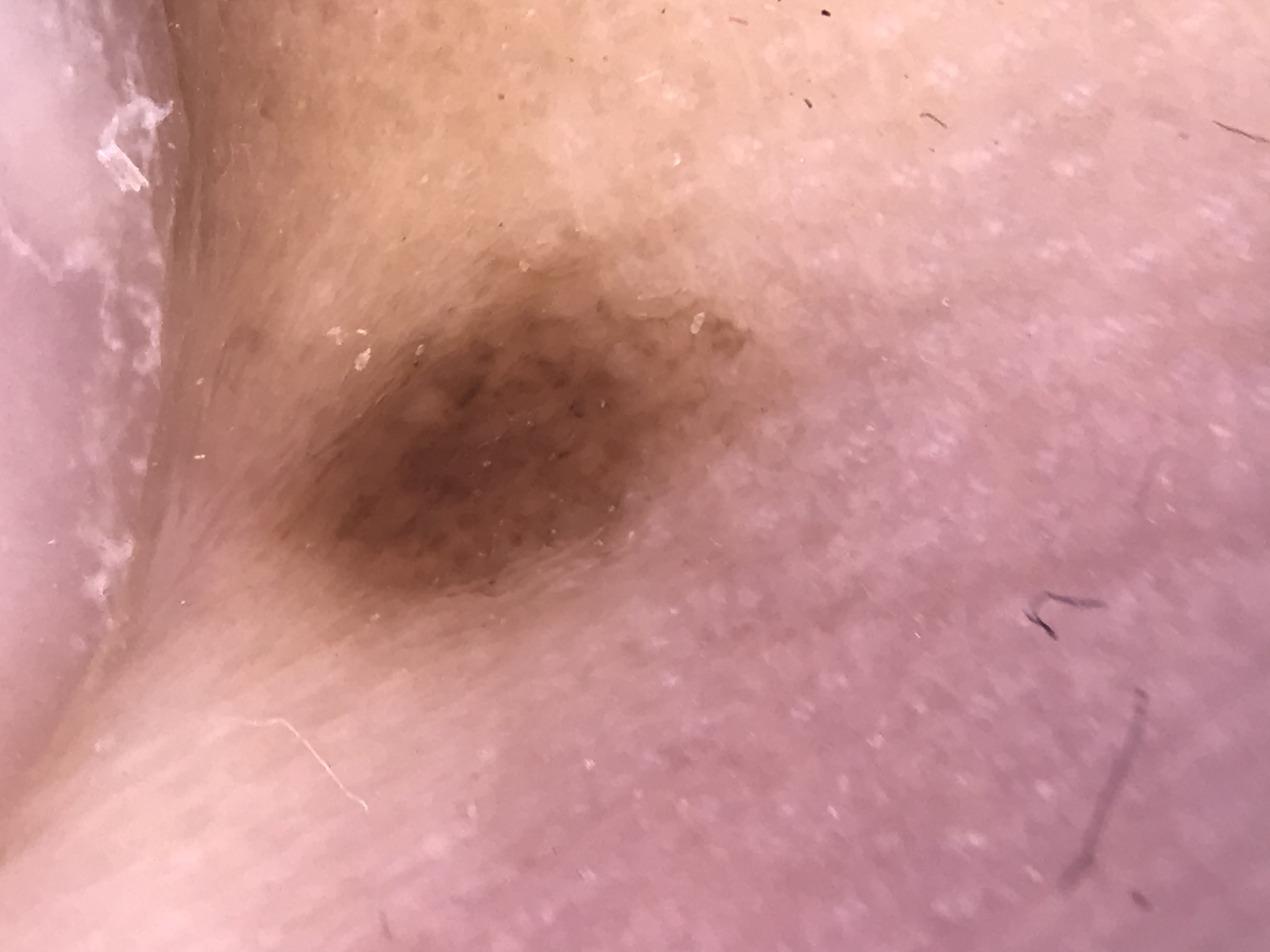The diagnosis was an acral junctional nevus.